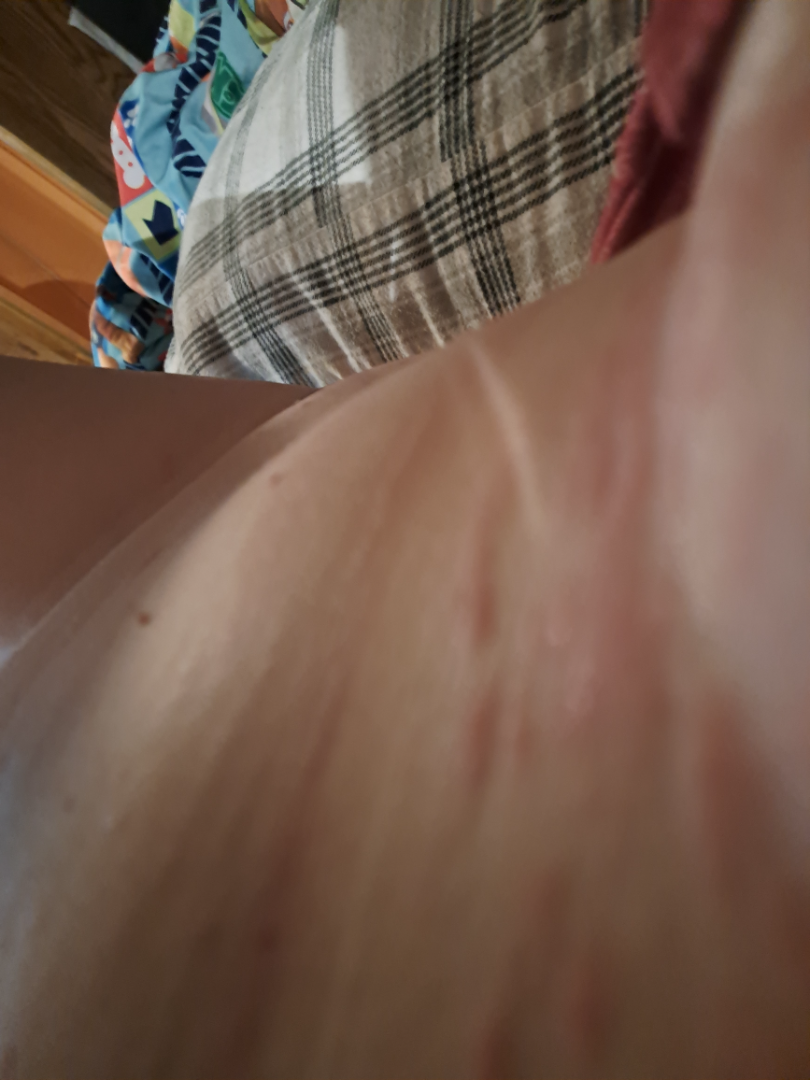The case was indeterminate on photographic review. Reported lesion symptoms include bothersome appearance and itching. Close-up view. The subject is female. No relevant systemic symptoms. Reported duration is less than one week. Texture is reported as raised or bumpy.